Dermoscopy of a skin lesion:
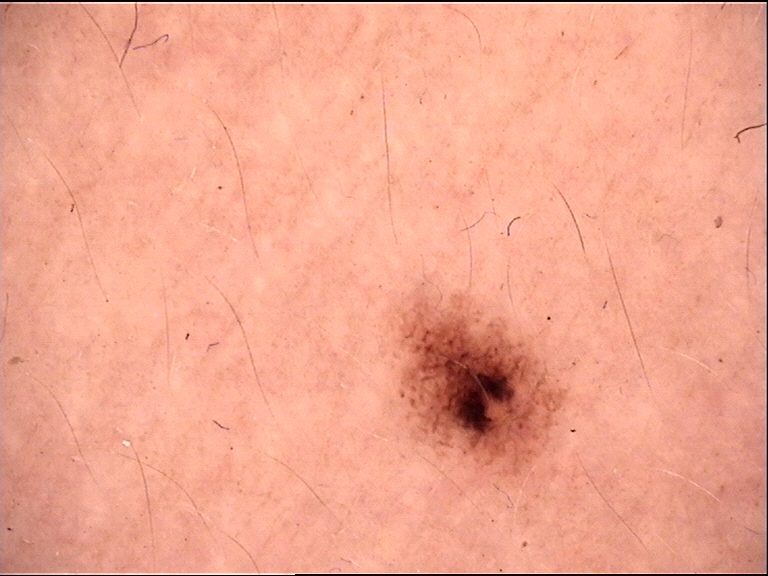Diagnosed as a benign lesion — a dysplastic junctional nevus.